The affected area is the arm. The patient is 18–29, female. Close-up view.
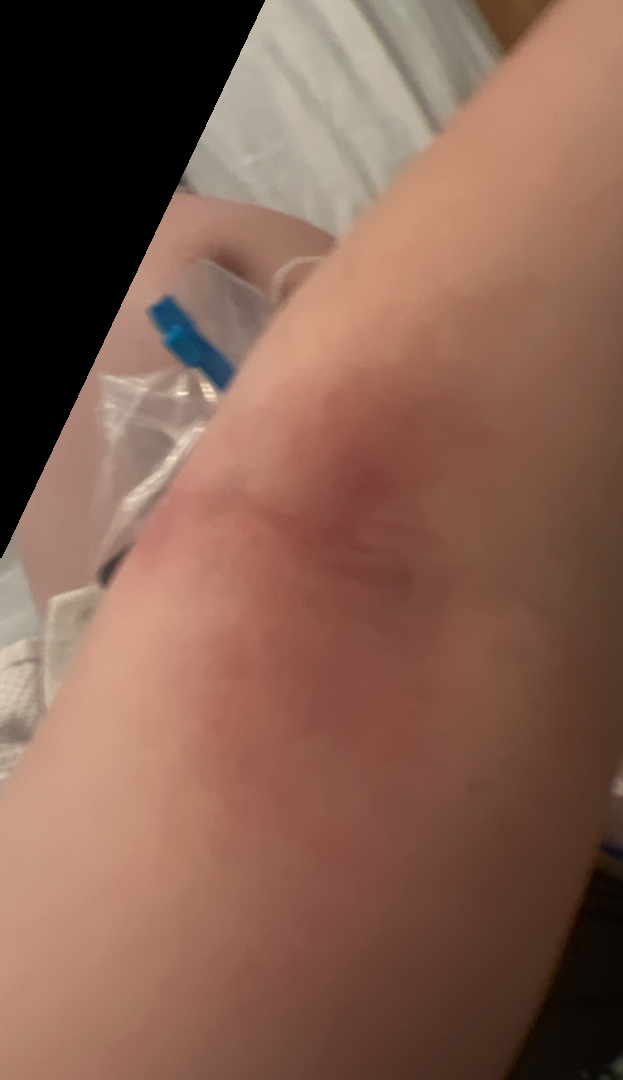Findings:
• assessment · unable to determine